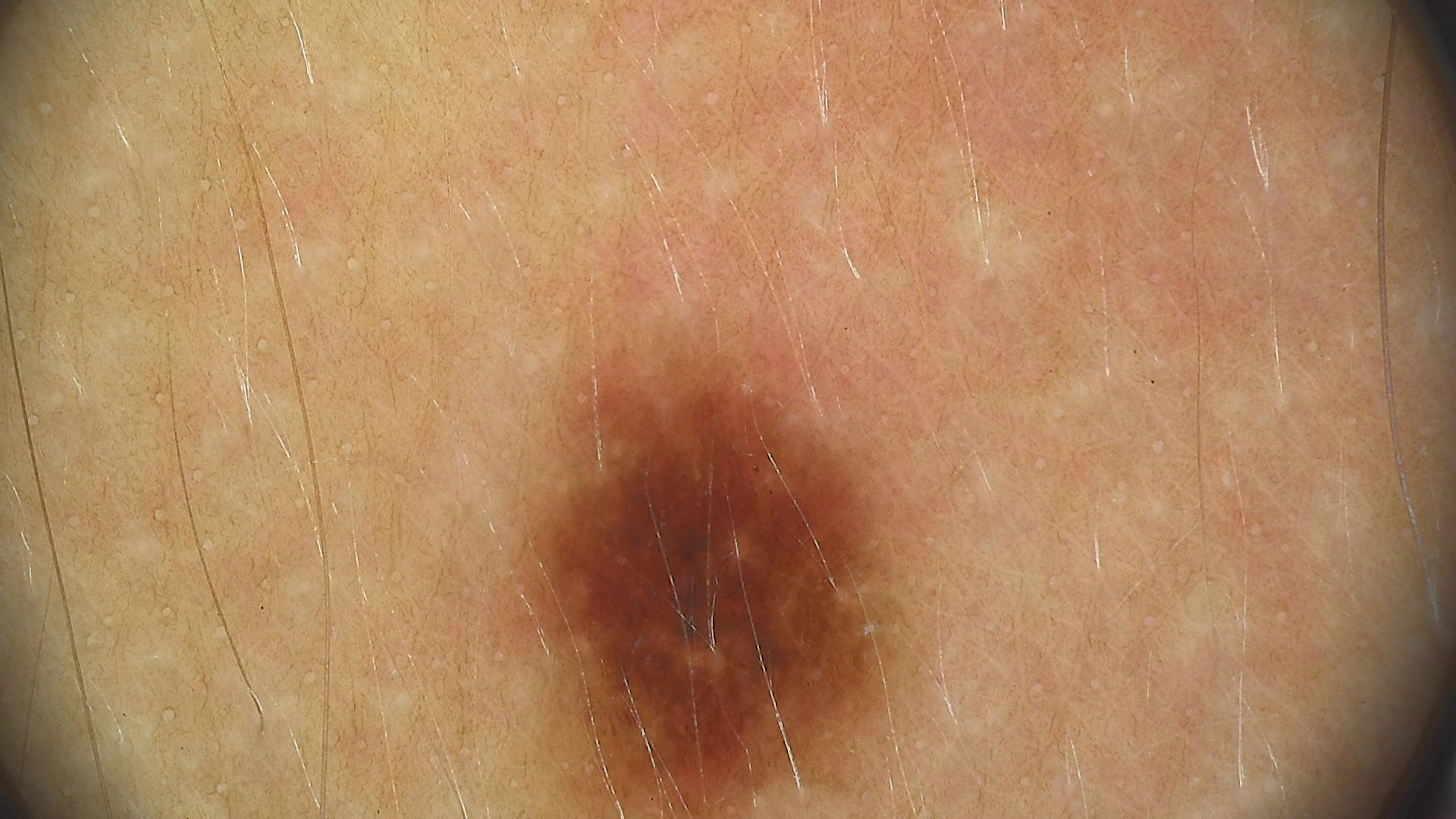Q: What is the imaging modality?
A: dermoscopy
Q: What is this lesion?
A: dysplastic junctional nevus (expert consensus)